The photo was captured at an angle · located on the leg.
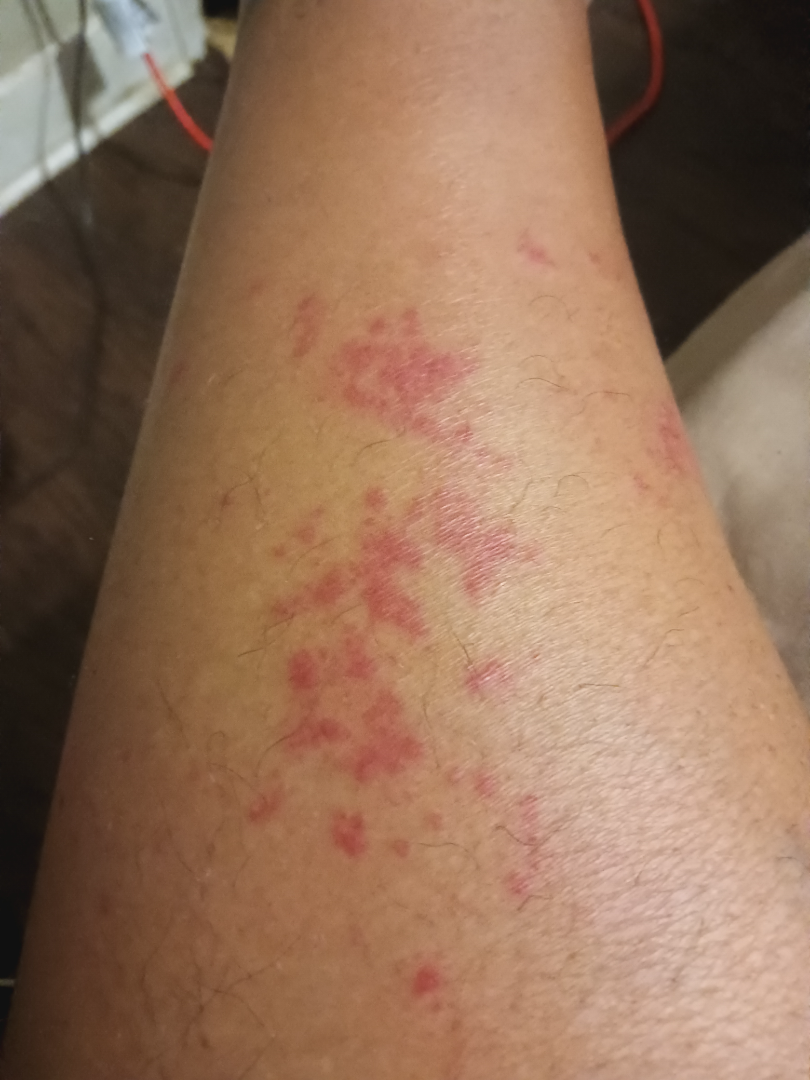The case was indeterminate on photographic review.